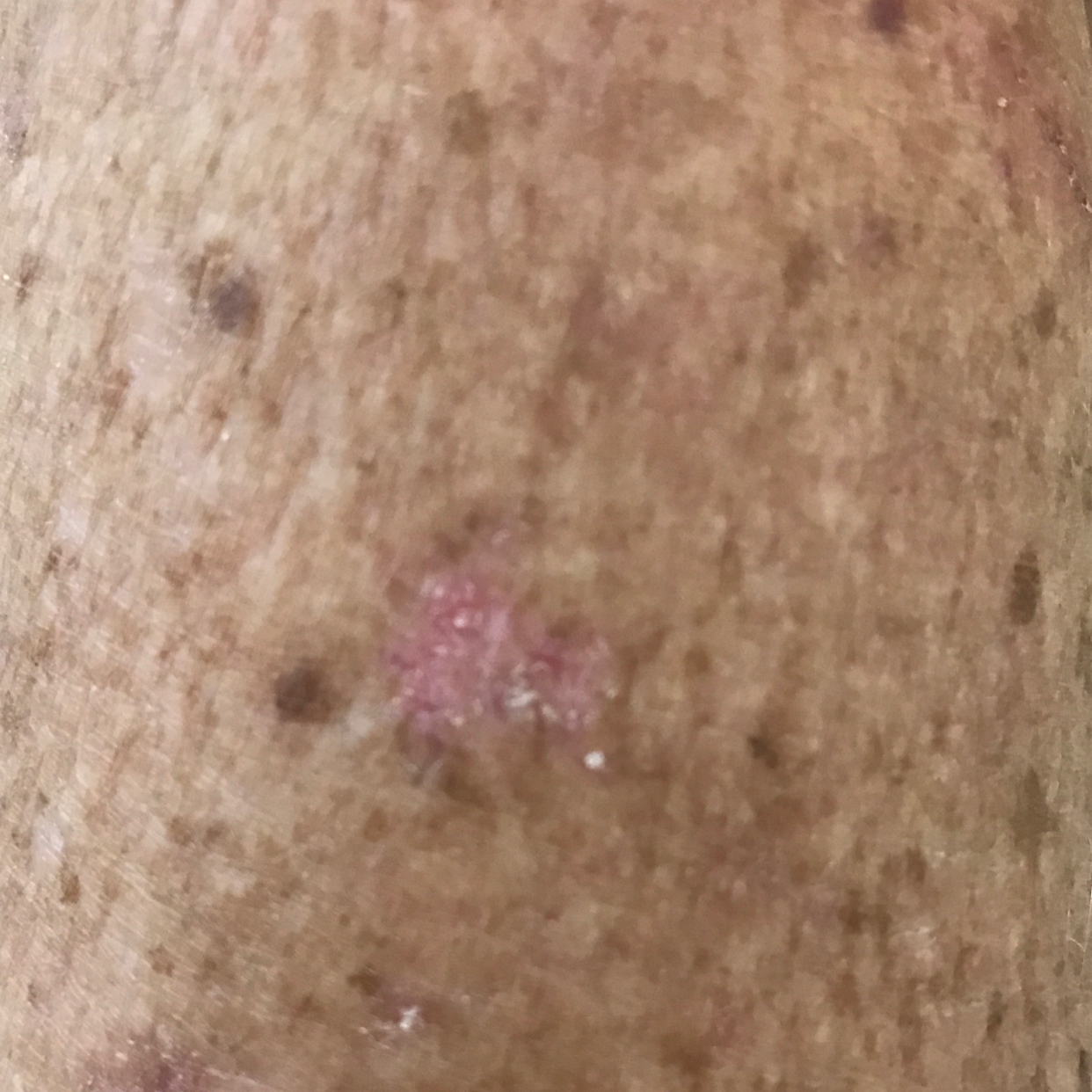<skin_lesion>
  <image>clinical photograph</image>
  <patient>
    <age>68</age>
  </patient>
  <lesion_location>a forearm</lesion_location>
  <symptoms>
    <present>elevation, itching</present>
    <absent>change in appearance</absent>
  </symptoms>
  <diagnosis>
    <name>actinic keratosis</name>
    <code>ACK</code>
    <malignancy>indeterminate</malignancy>
    <confirmation>clinical consensus</confirmation>
  </diagnosis>
</skin_lesion>